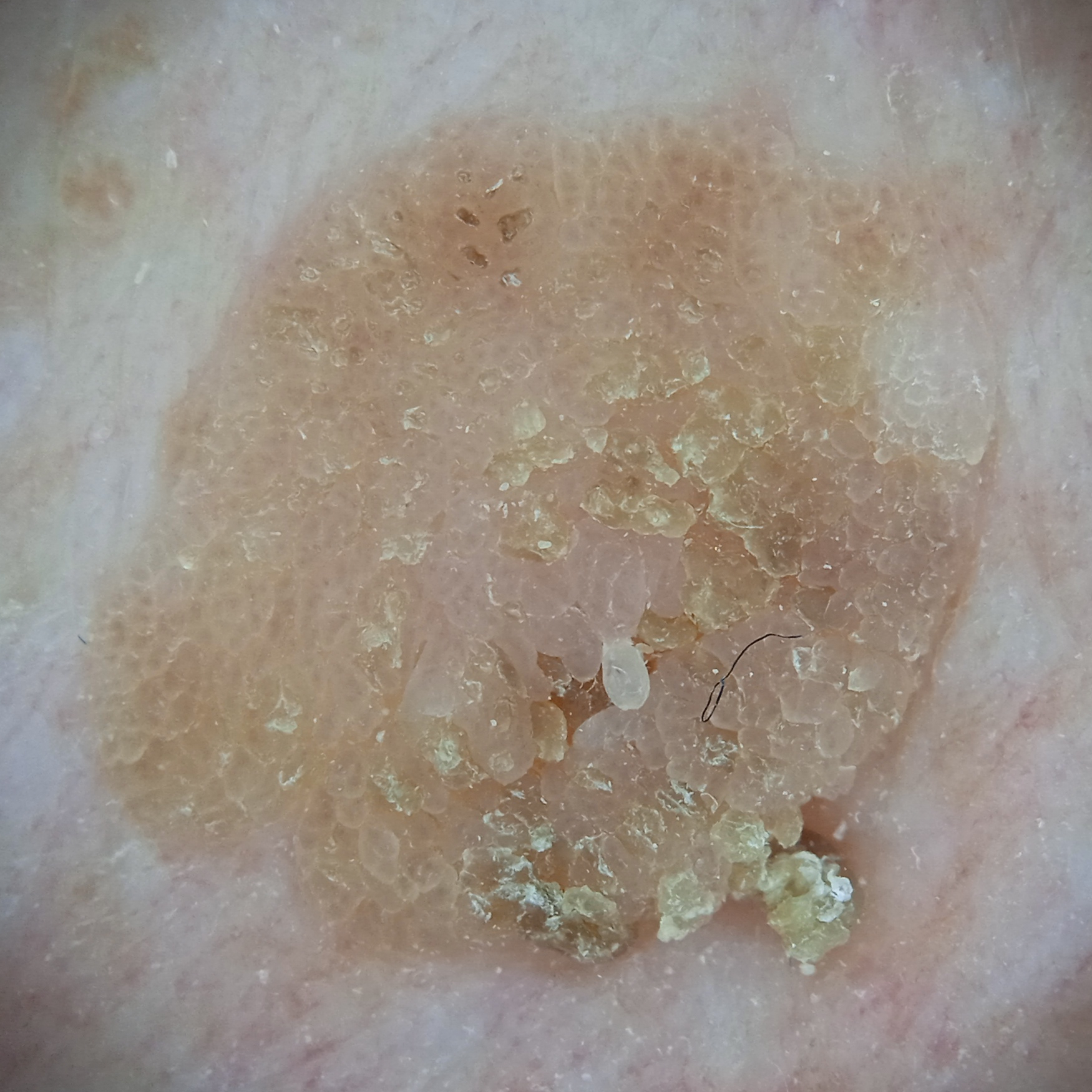Q: How does the patient's skin react to sun?
A: skin reddens with sun exposure
Q: What is the patient's nevus burden?
A: few melanocytic nevi overall
Q: Tell me about the patient.
A: male, 62 years old
Q: What is the imaging modality?
A: dermatoscopic image
Q: Where is the lesion?
A: the torso
Q: How large is the lesion?
A: 11.3 mm
Q: What was the diagnosis?
A: seborrheic keratosis (dermatologist consensus)